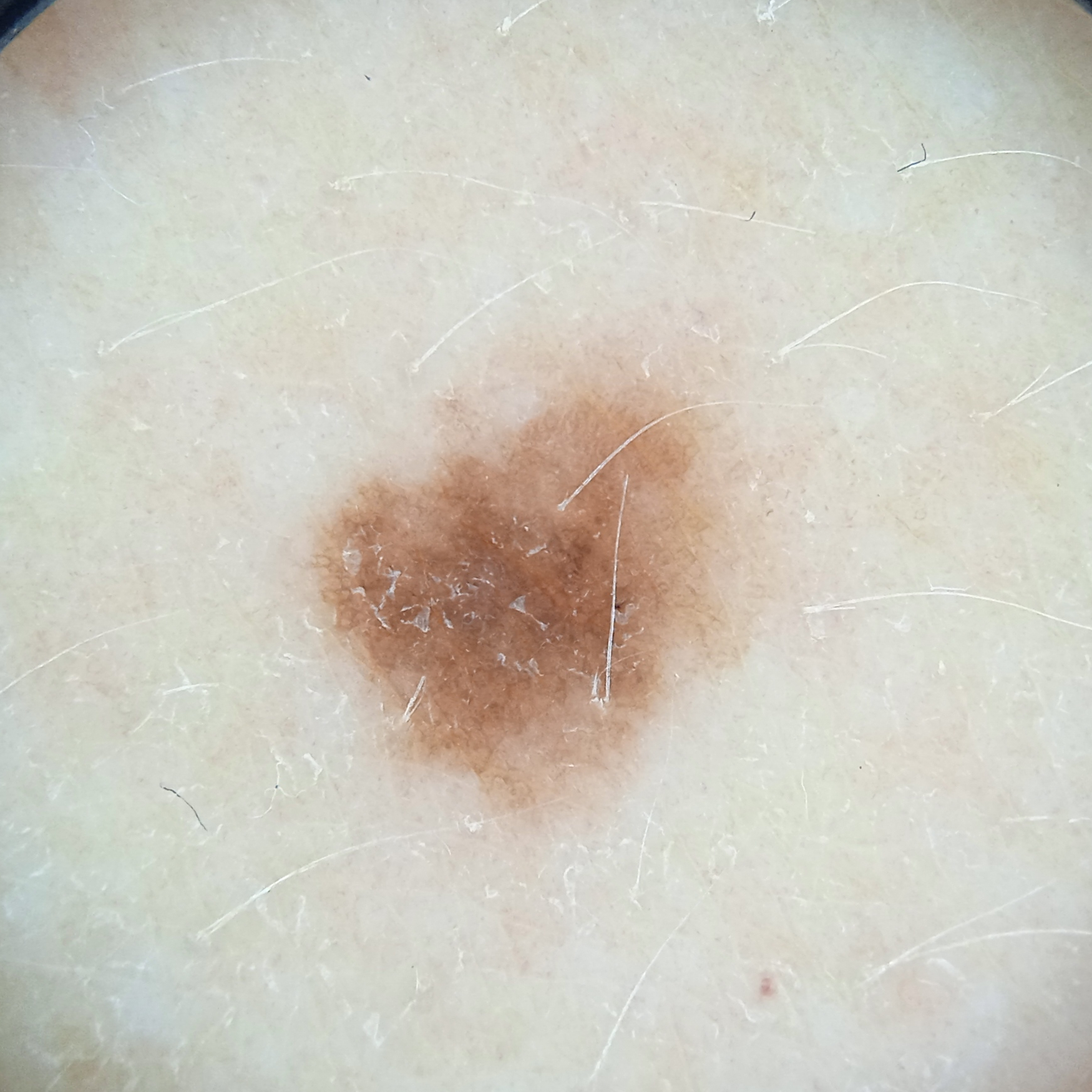| field | value |
|---|---|
| referral | research study (no referral diagnosis) |
| diameter | 5.4 mm |
| assessment | melanocytic nevus (dermatologist consensus) |